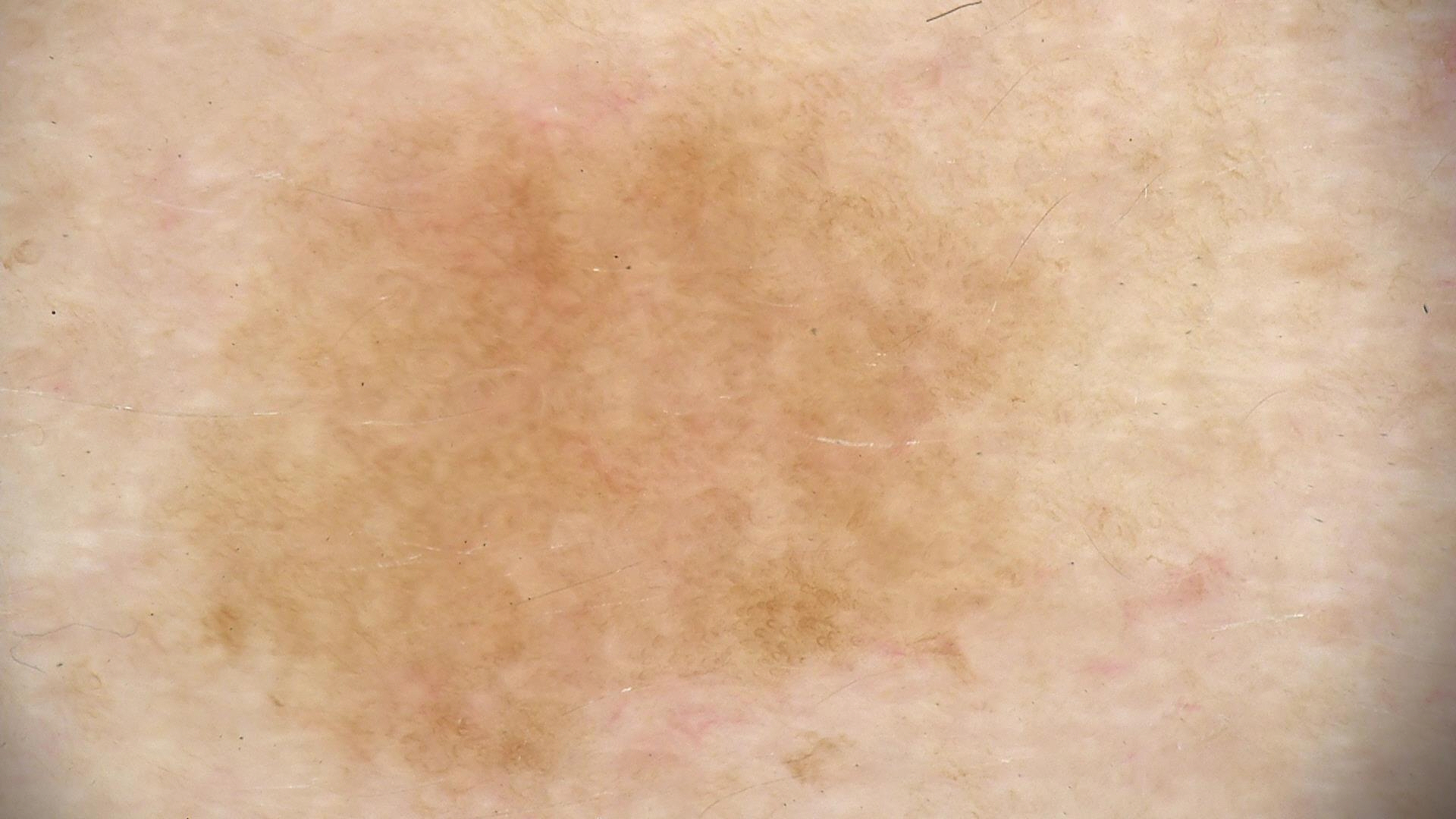The diagnostic label was a benign lesion — a solar lentigo.